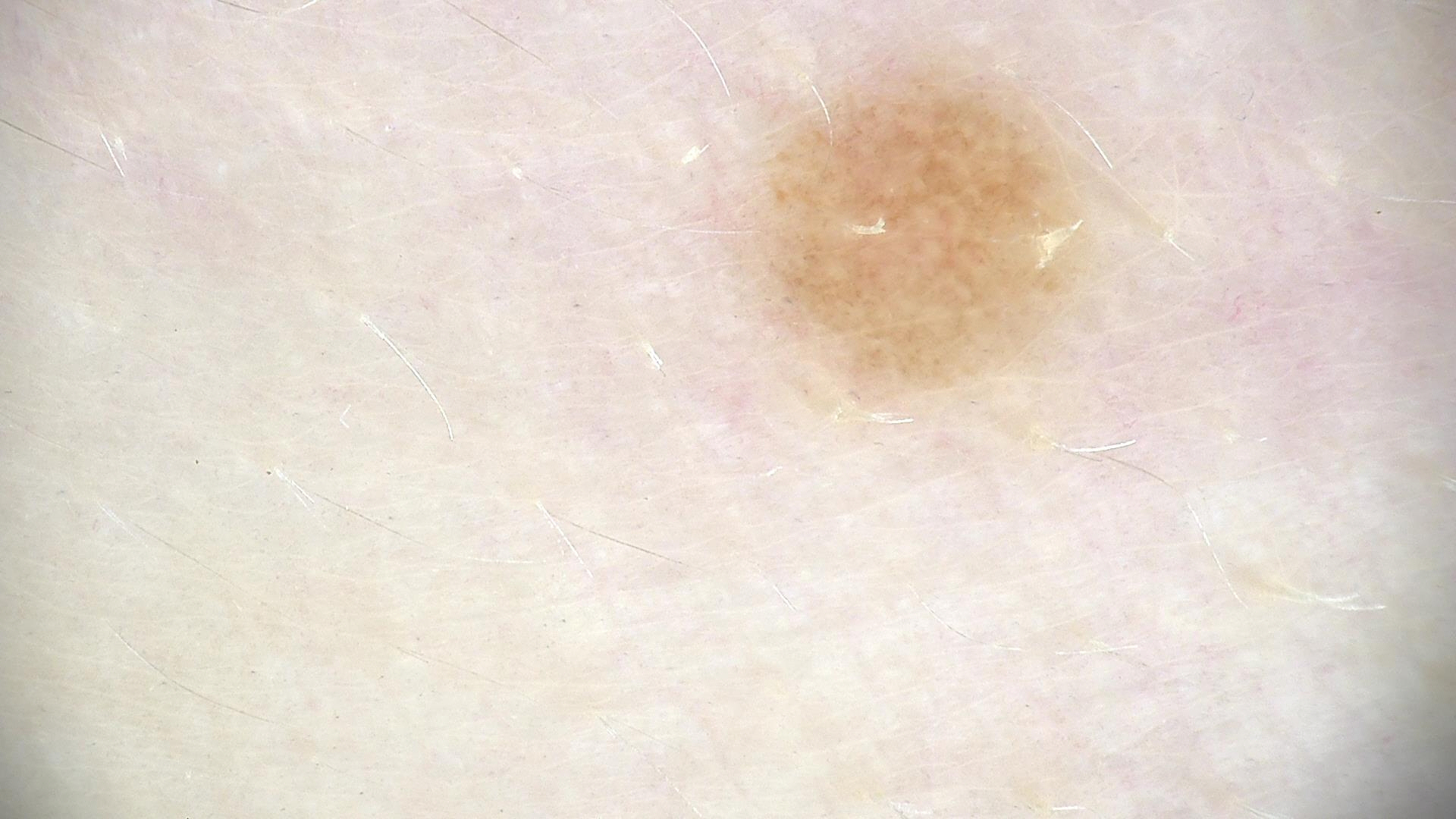diagnostic label: dysplastic junctional nevus (expert consensus).